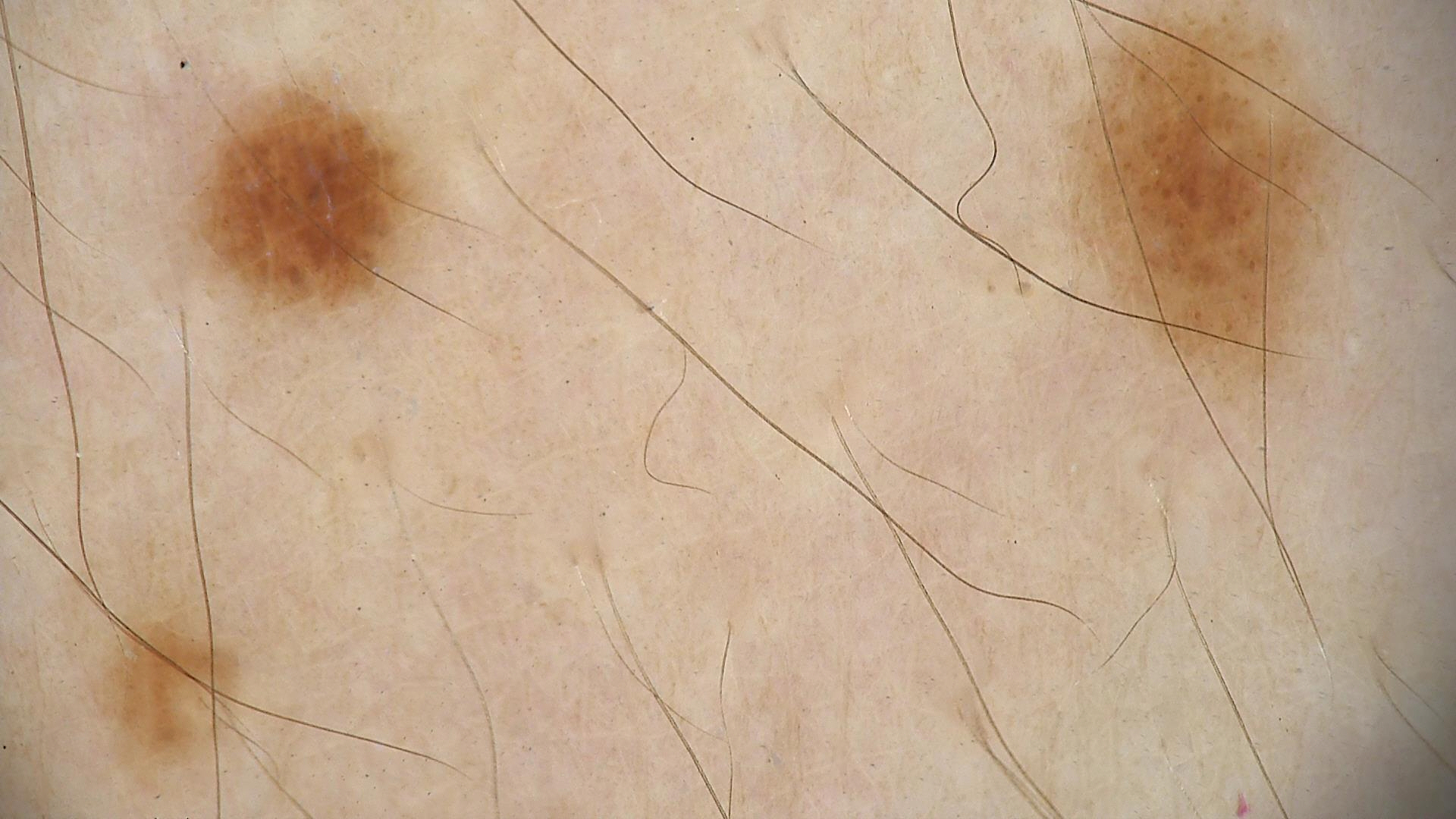A dermatoscopic image of a skin lesion. Classified as a benign lesion — a dysplastic junctional nevus.